Dermoscopy of a skin lesion: 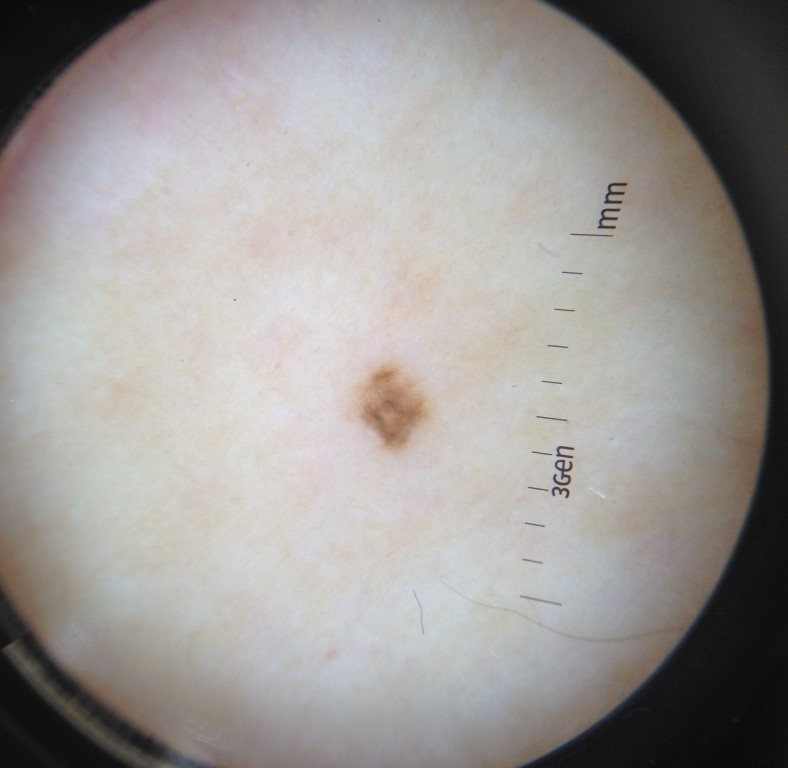Conclusion: Diagnosed as a dysplastic junctional nevus.